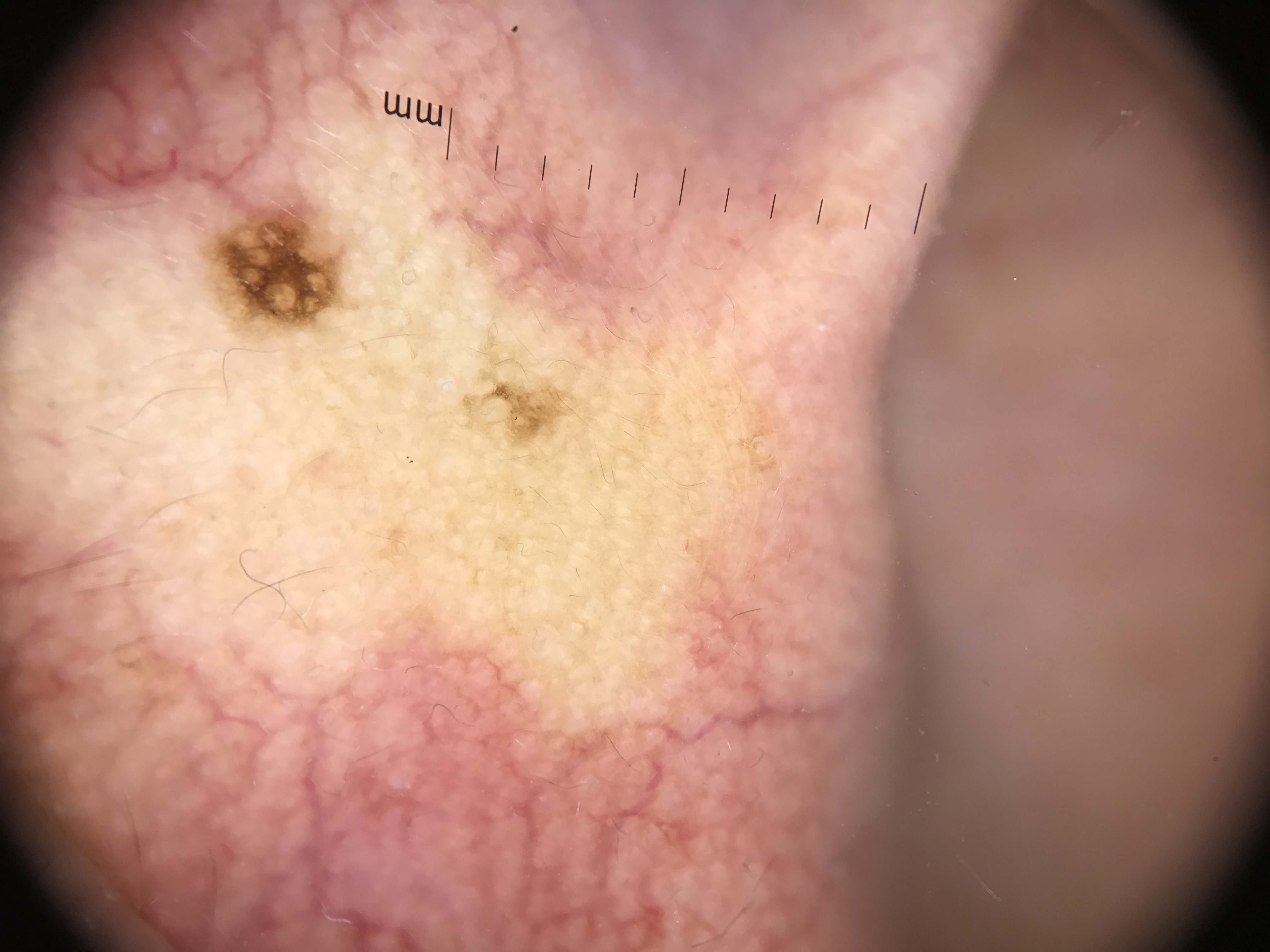Labeled as a dysplastic junctional nevus.